A male patient roughly 45 years of age · a dermatoscopic image of a skin lesion:
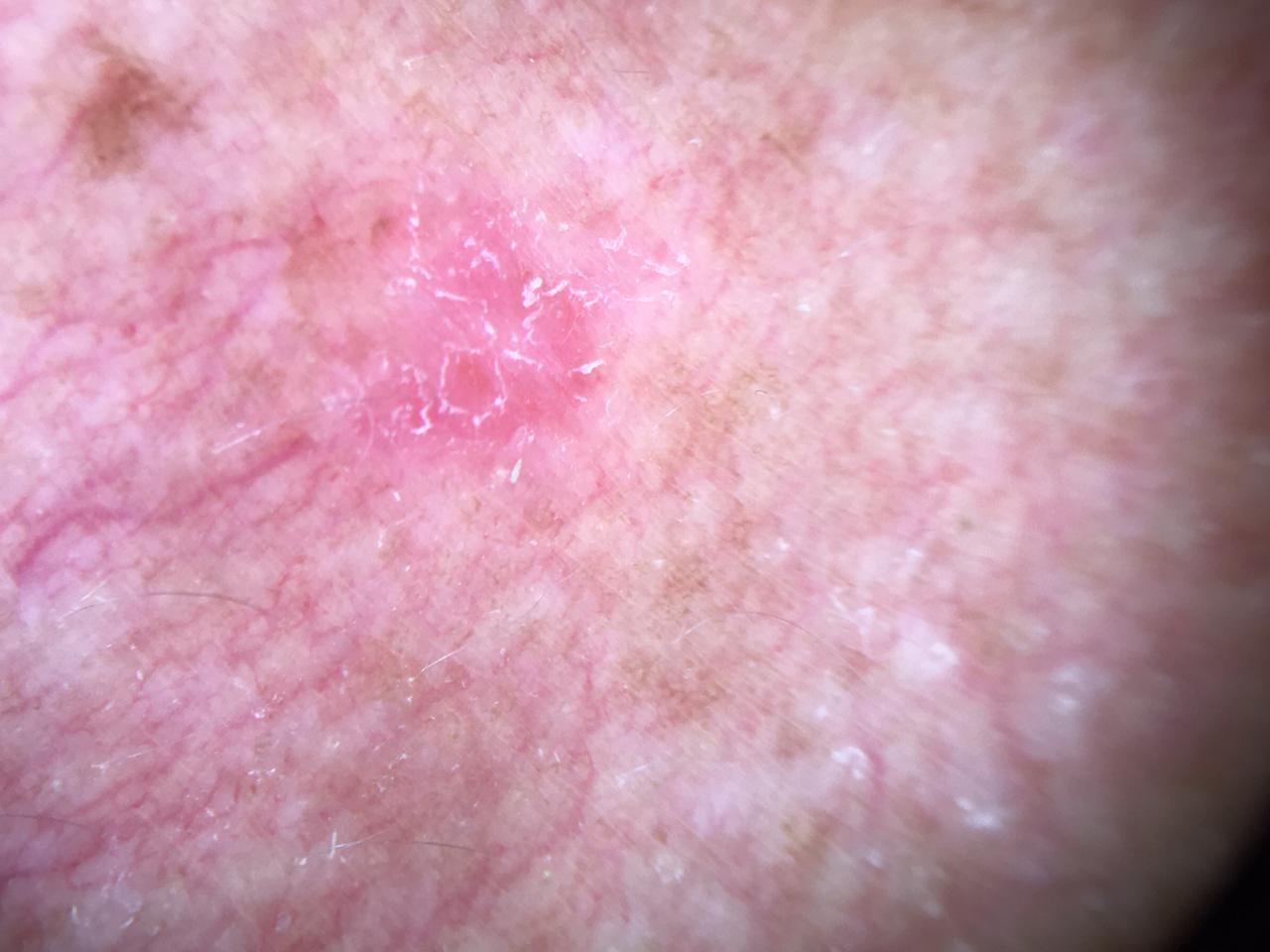The lesion involves the trunk.
Histopathology confirmed a basal cell carcinoma.